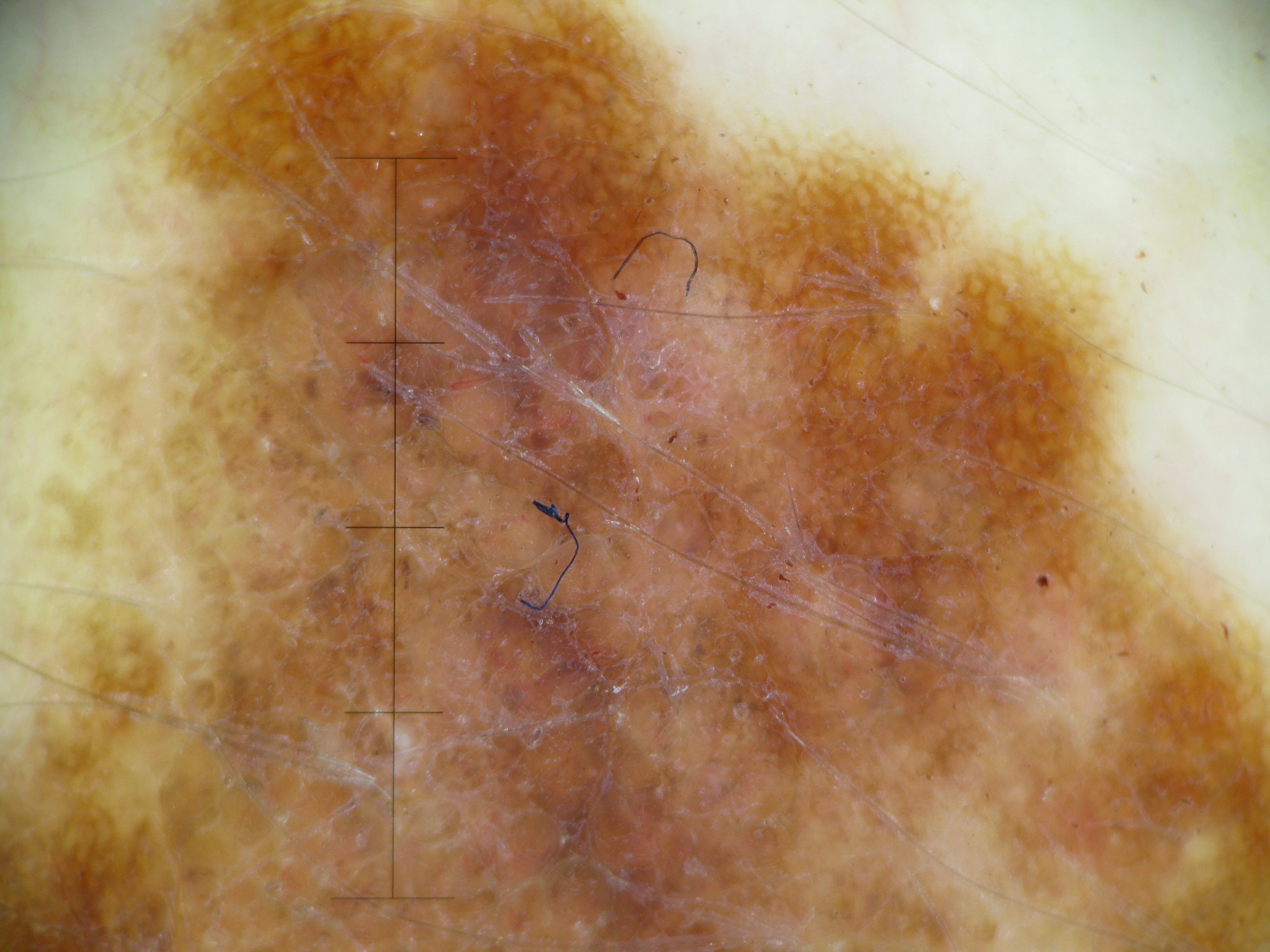| key | value |
|---|---|
| image type | dermatoscopy |
| diagnostic label | melanoma (biopsy-proven) |